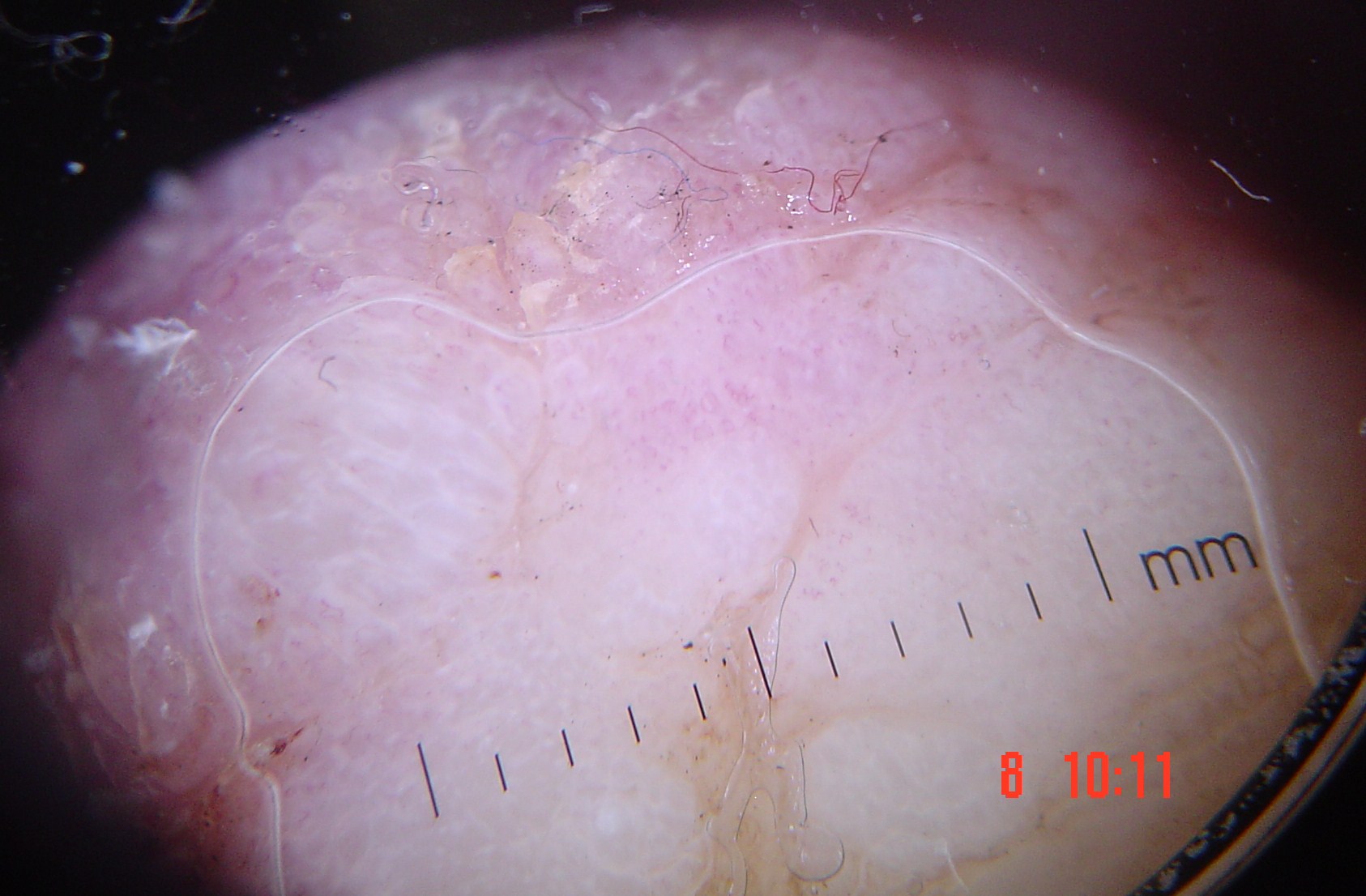The biopsy diagnosis was a skin cancer — an acral nodular melanoma.